The contributor is 50–59, female · the condition has been present for more than five years · this image was taken at an angle · the lesion is described as raised or bumpy · the patient reported no relevant symptoms from the lesion · the affected area is the leg:
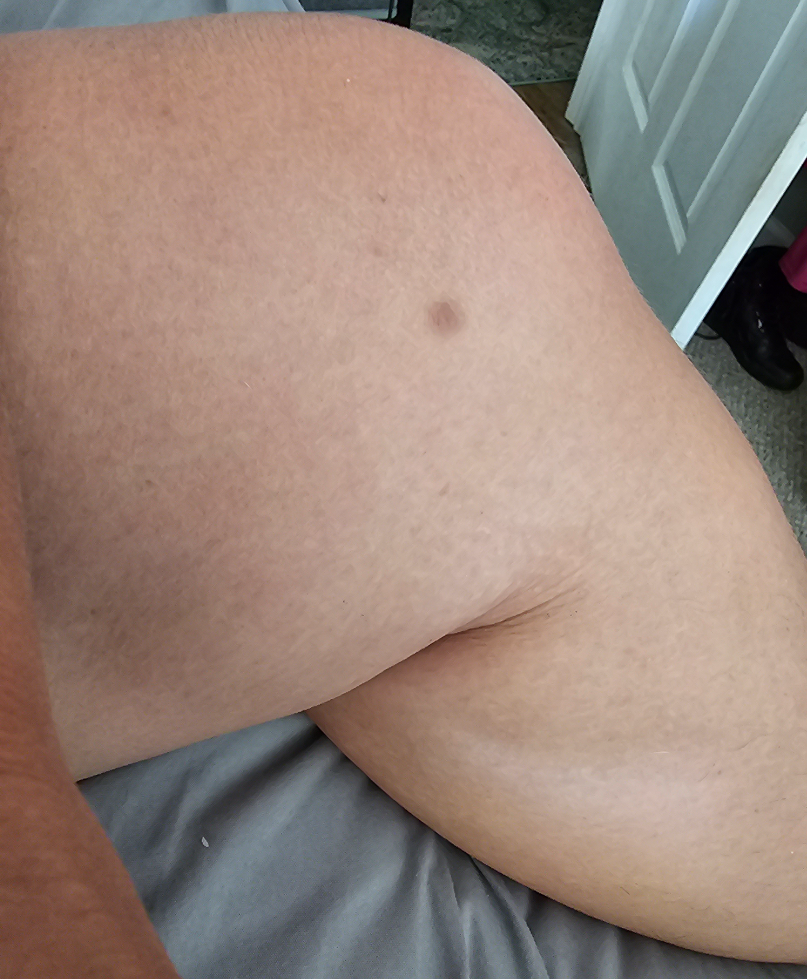dermatologist impression = the favored diagnosis is Dermatofibroma; a more distant consideration is Melanocytic Nevus; lower on the differential is Lichen Simplex Chronicus.